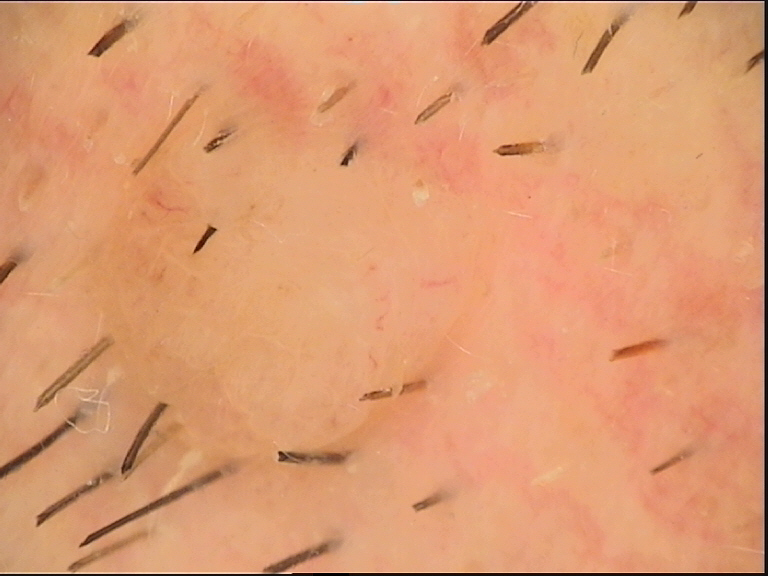Diagnosed as a dermal nevus.